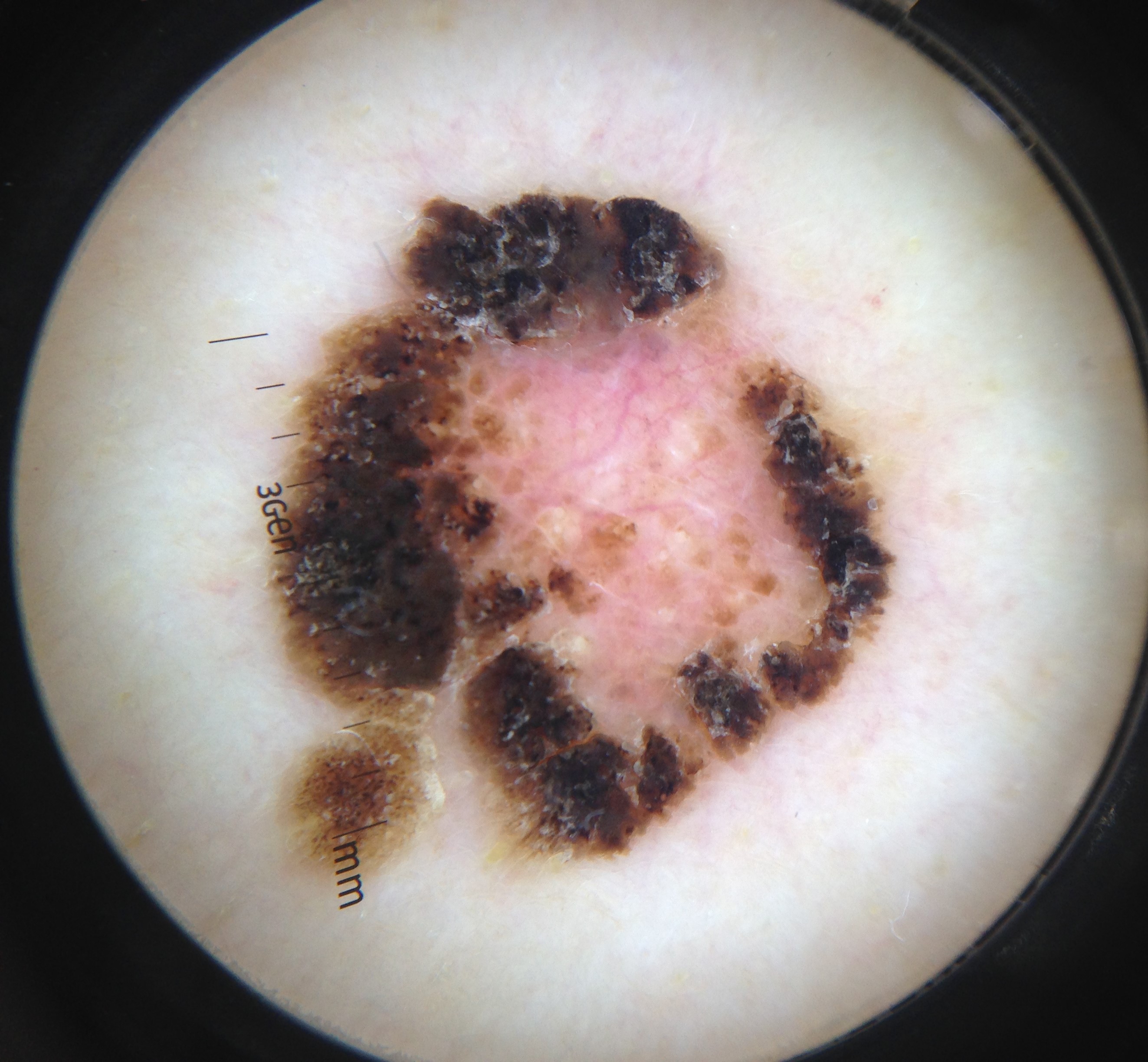Dermoscopy of a skin lesion. The architecture is that of a keratinocytic lesion. Labeled as a seborrheic keratosis.